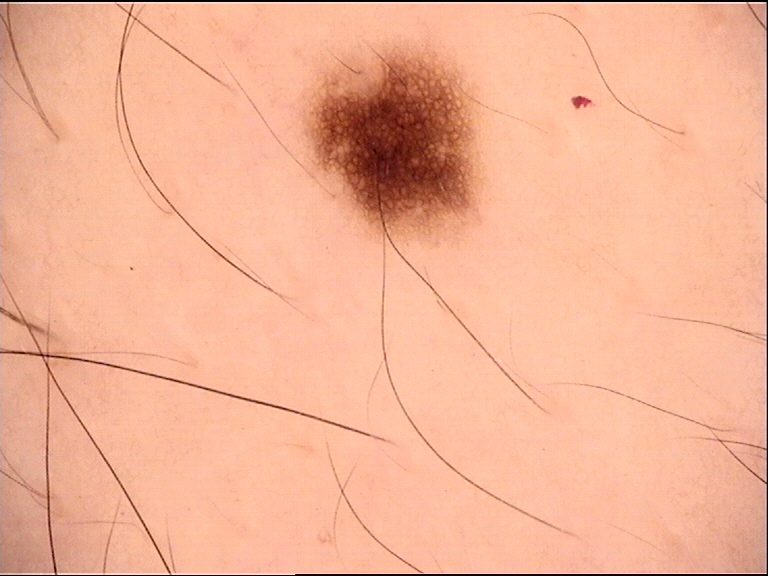label: junctional nevus (expert consensus).